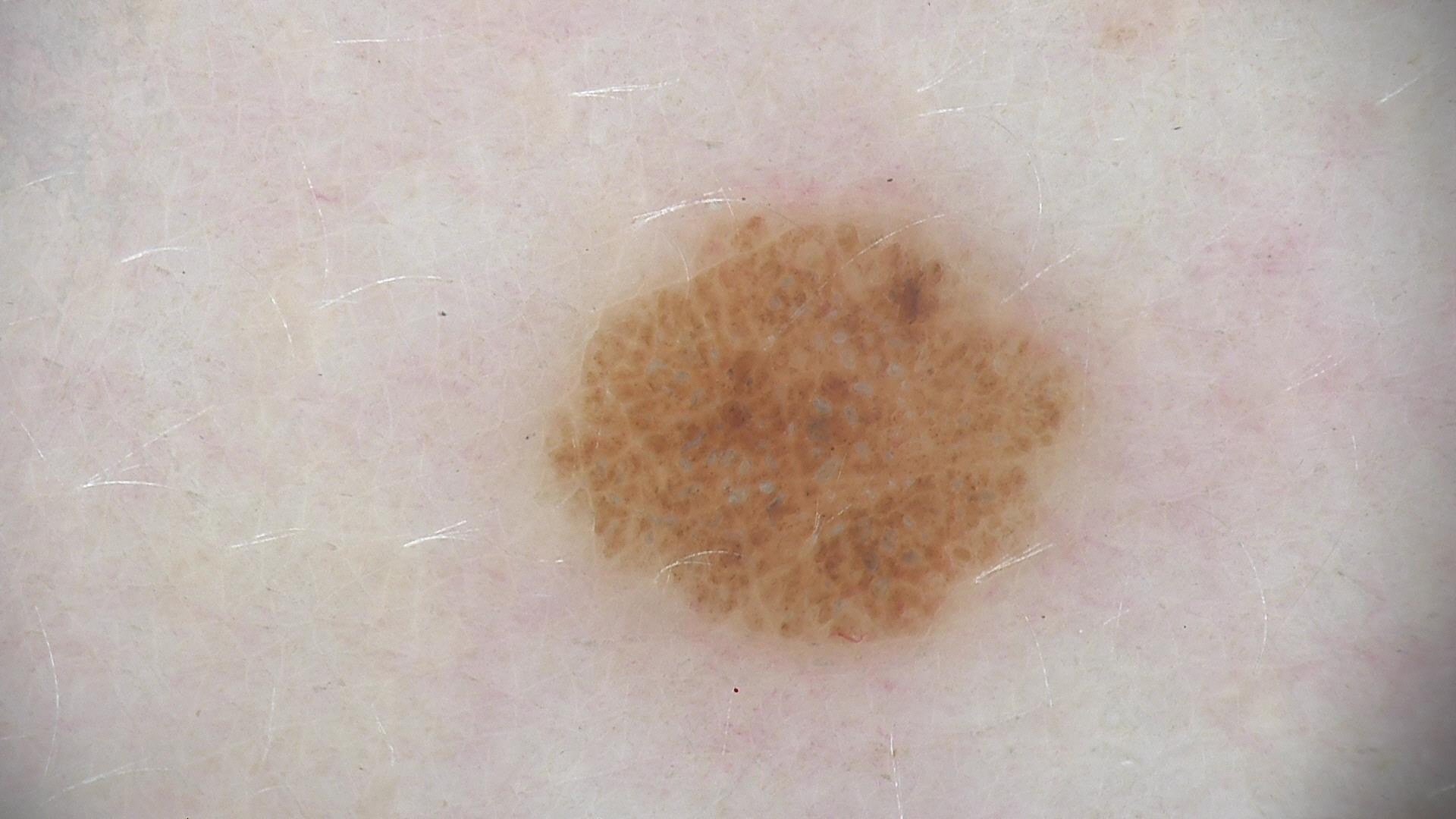class — compound nevus (expert consensus).